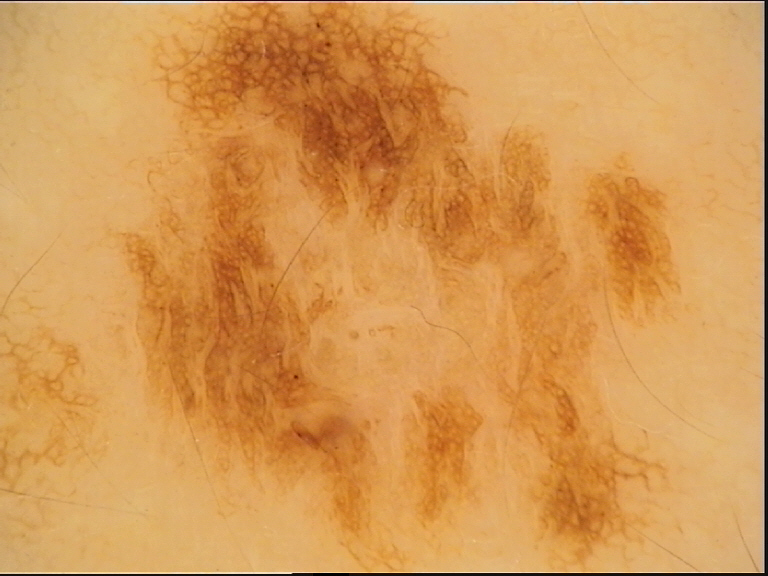| feature | finding |
|---|---|
| modality | dermoscopy |
| assessment | dysplastic junctional nevus (expert consensus) |